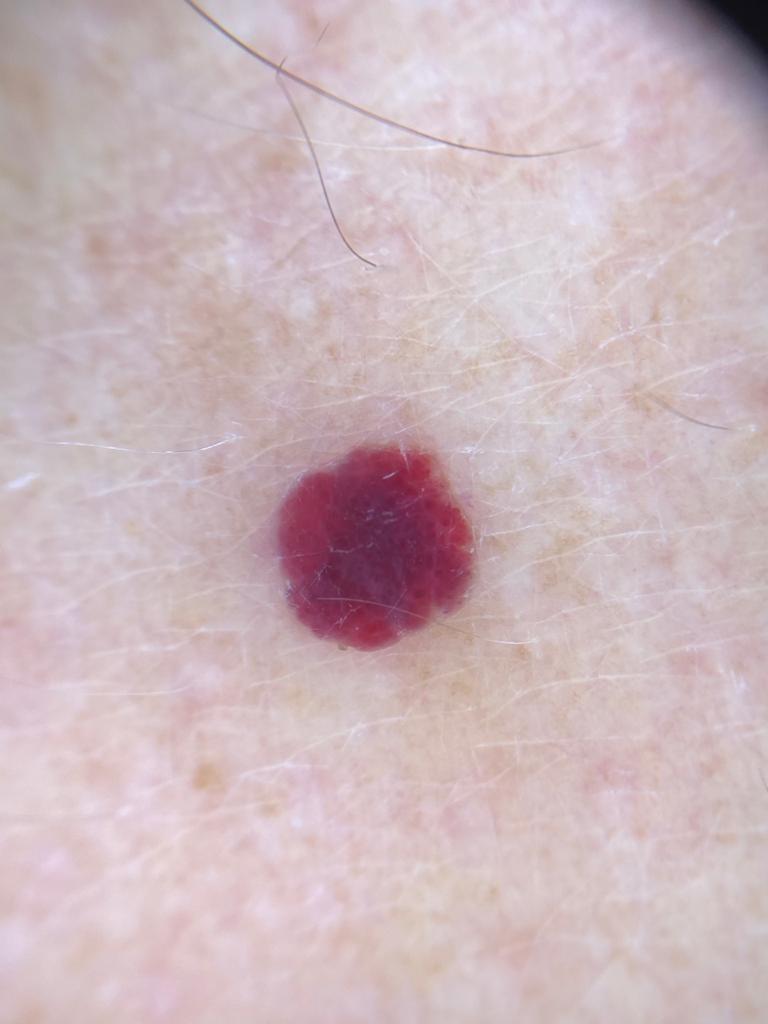Clinical context: FST II. A dermoscopic photograph of a skin lesion. A male patient aged 73-77. Located on the anterior trunk. Conclusion: The clinical impression was a vascular lesion.